This is a dermoscopic photograph of a skin lesion — 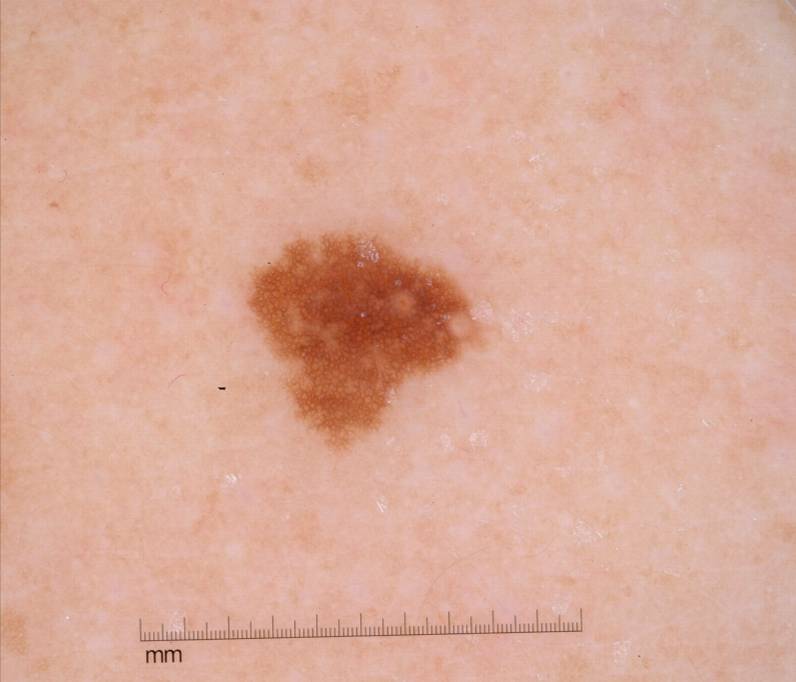In (x1, y1, x2, y2) order, the lesion's extent is <bbox>244, 227, 482, 450</bbox>.
Dermoscopic review identifies pigment network; no globules, streaks, negative network, or milia-like cysts.
The clinical diagnosis was a melanocytic nevus, a benign skin lesion.